Self-categorized by the patient as a rash. Close-up view. The lesion involves the arm. No associated systemic symptoms reported. The lesion is associated with itching, bothersome appearance and enlargement. Male contributor, age 30–39. Texture is reported as raised or bumpy.
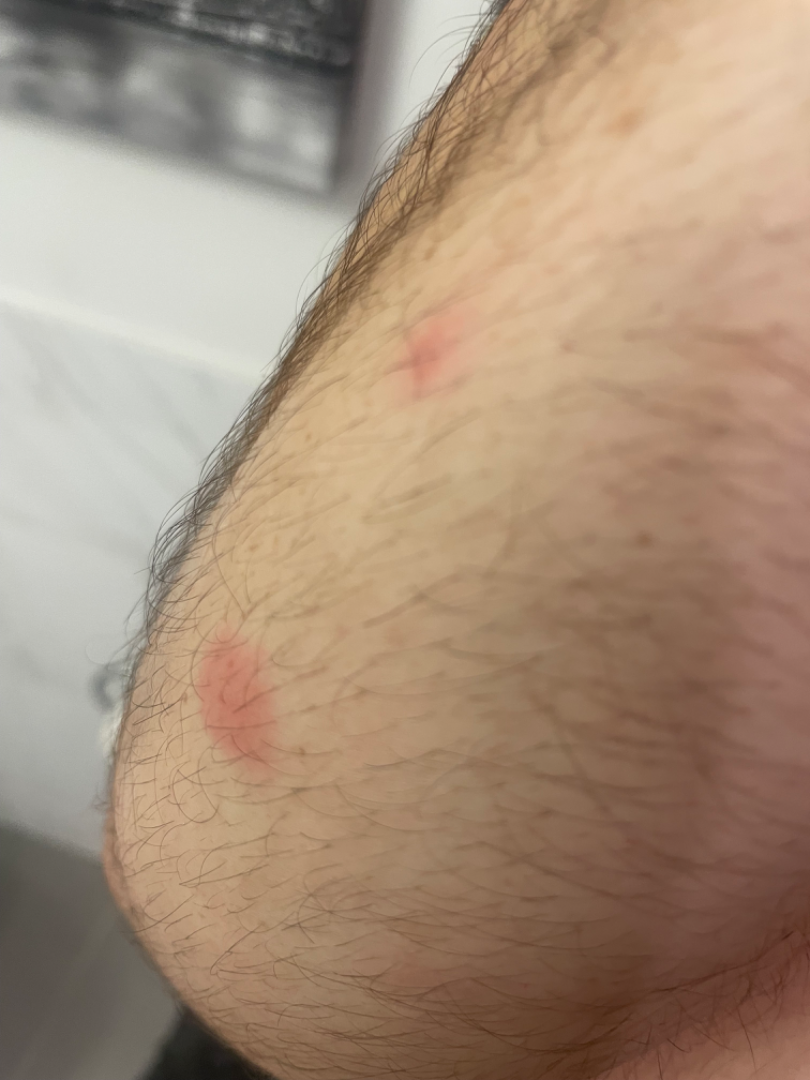assessment: indeterminate.